The photo was captured at a distance — 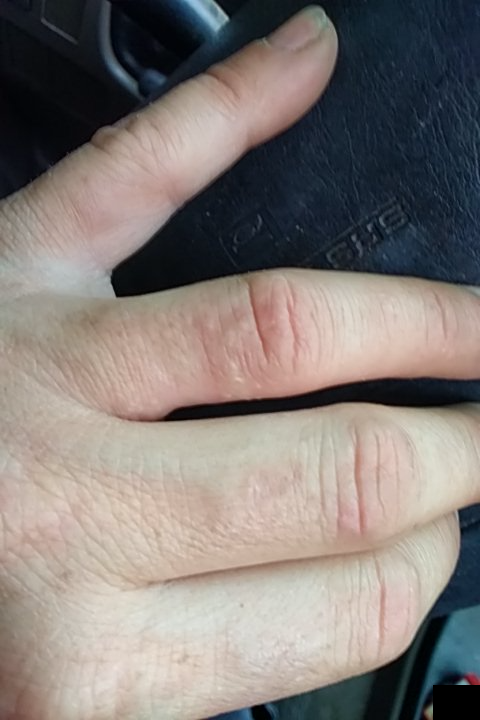Review:
No differential diagnosis could be assigned on photographic review.